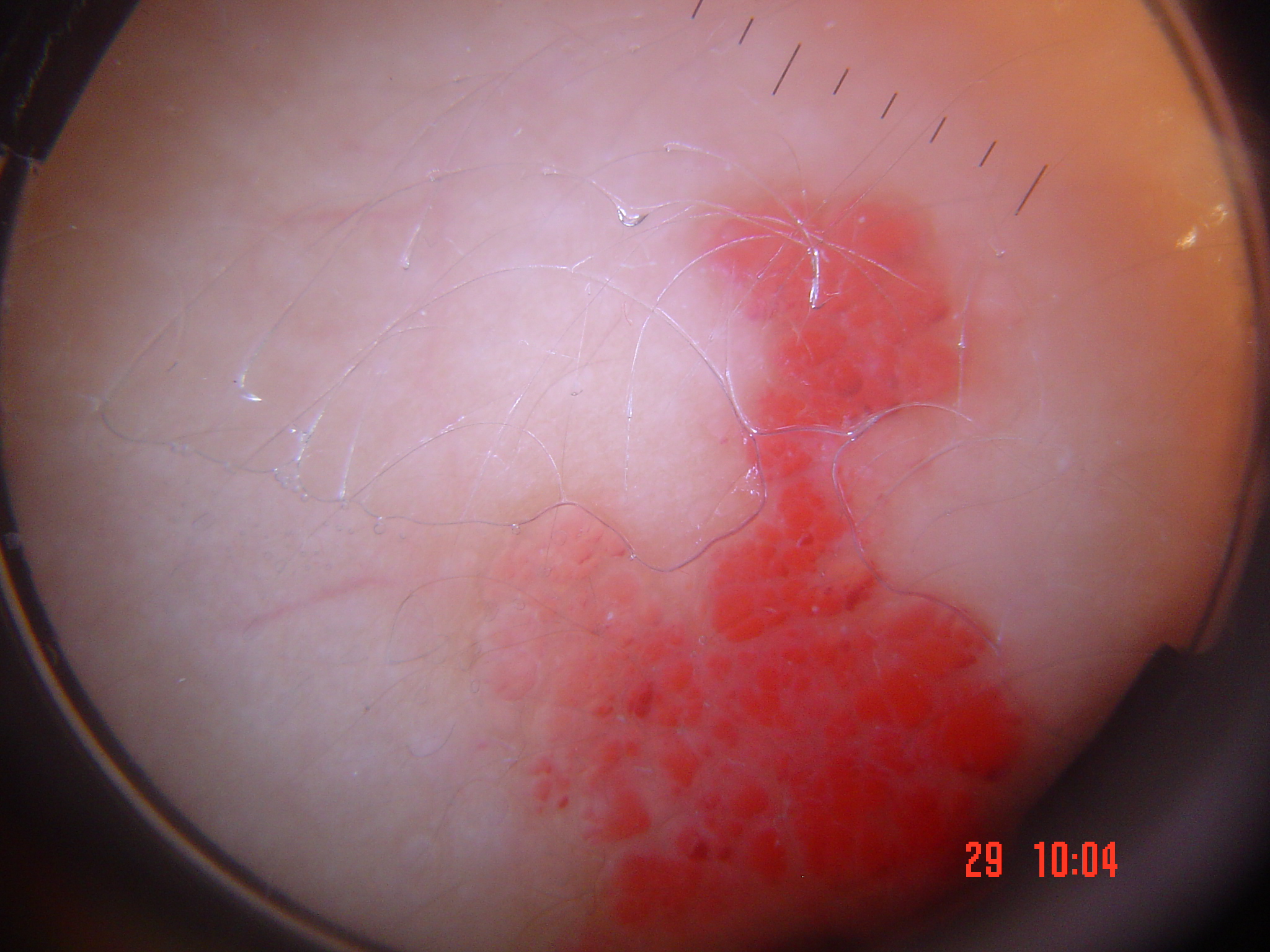A dermoscopic close-up of a skin lesion. Labeled as a vascular, benign lesion — a lymphangioma.